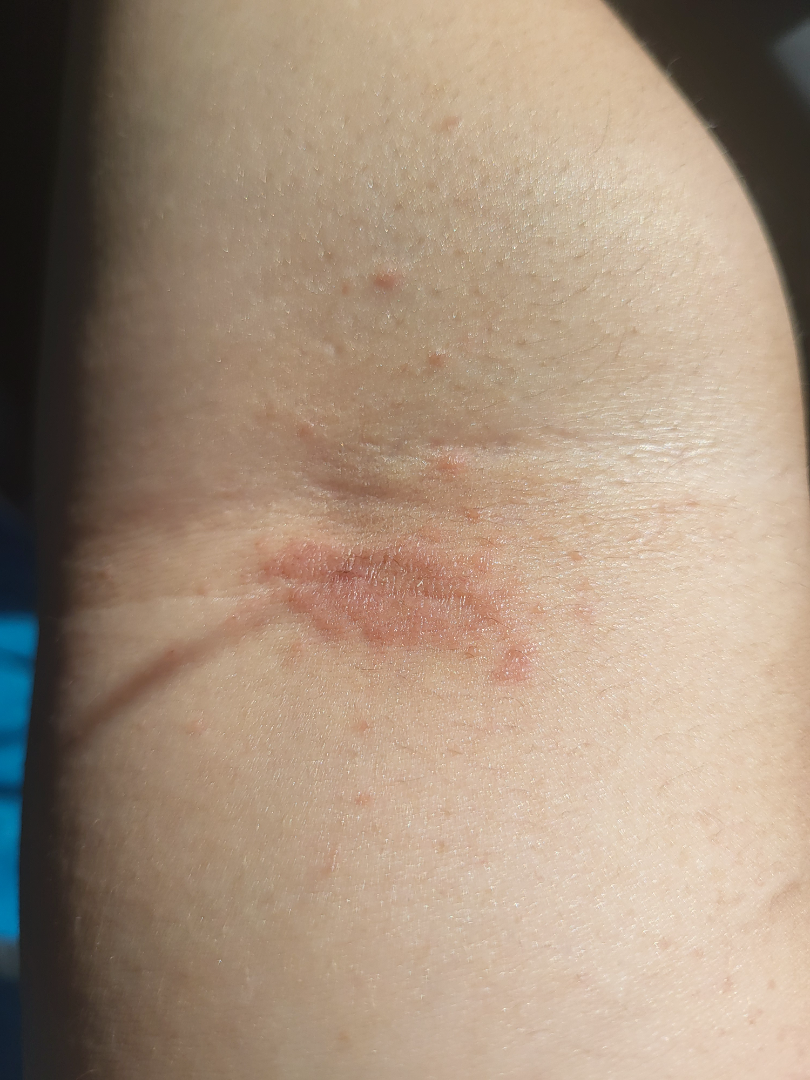History: The affected area is the arm. Texture is reported as raised or bumpy and rough or flaky. Symptoms reported: burning, bothersome appearance, darkening, enlargement and itching. Present for one to four weeks. An image taken at an angle. Impression: On remote dermatologist review, Eczema (primary); Intertrigo (possible); Tinea (lower probability); Psoriasis (lower probability).